A dermoscopy image of a single skin lesion.
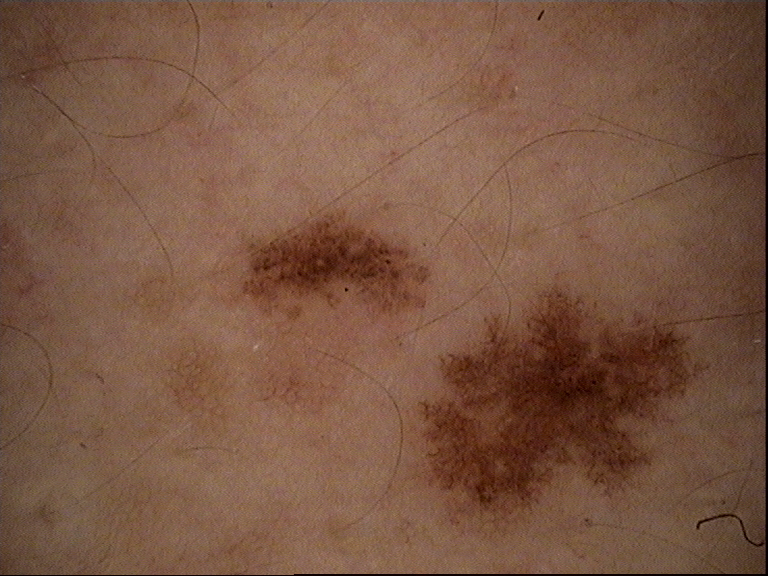{"diagnosis": {"name": "dysplastic junctional nevus", "code": "jd", "malignancy": "benign", "super_class": "melanocytic", "confirmation": "expert consensus"}}